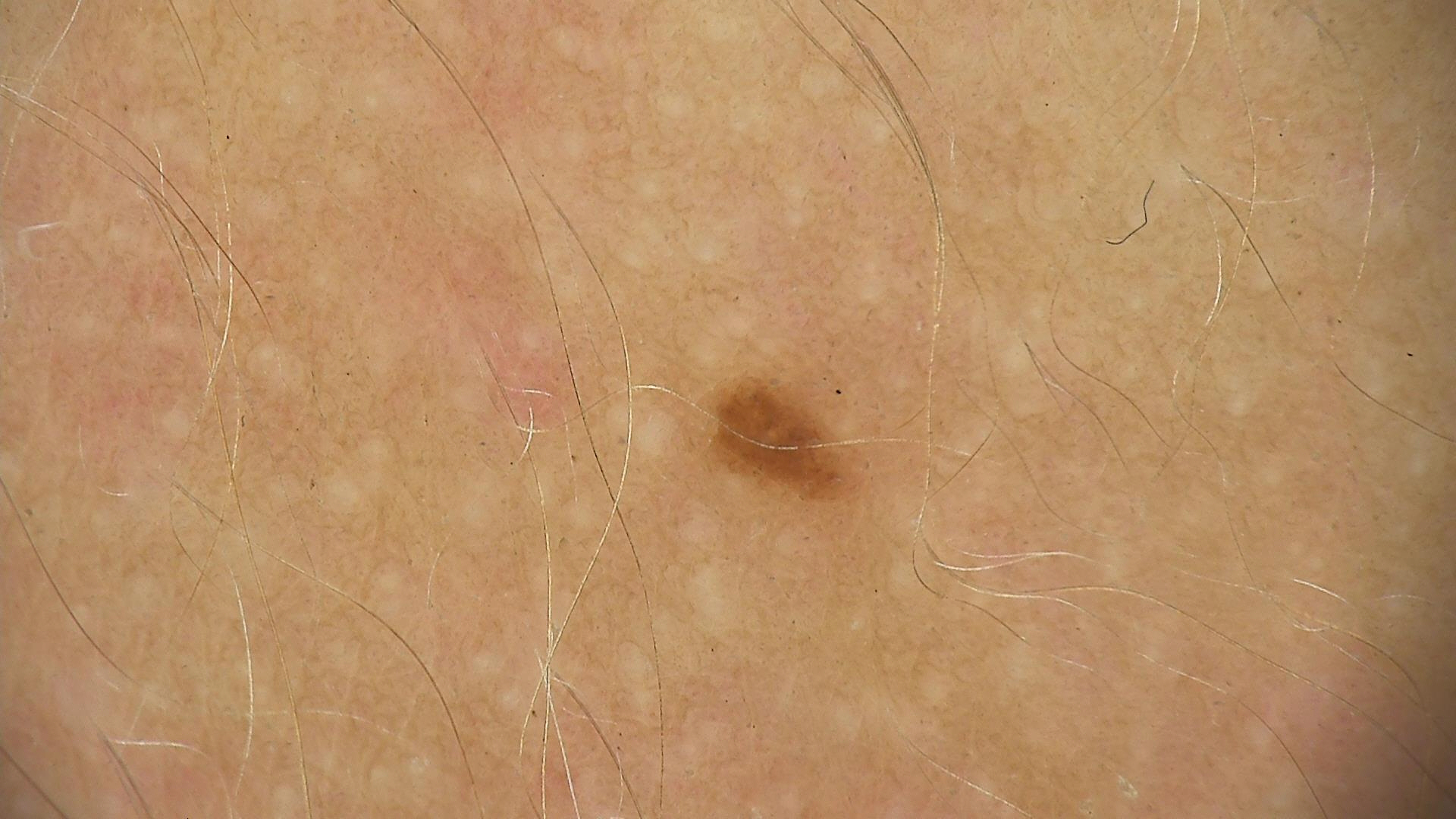Summary: A dermatoscopic image of a skin lesion. Impression: Diagnosed as a benign lesion — a dysplastic junctional nevus.